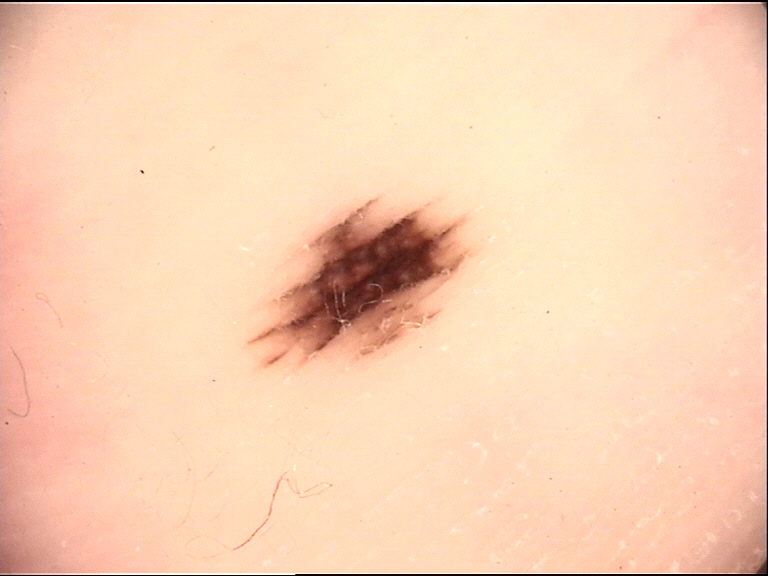imaging: dermoscopy | classification: banal | class: acral junctional nevus (expert consensus).